The lesion involves the arm, back of the torso and leg. The patient reported no systemic symptoms. Present for about one day. The patient notes the lesion is flat. Female contributor, age 18–29. Symptoms reported: itching and bothersome appearance. Self-categorized by the patient as a rash. The photograph was taken at an angle — 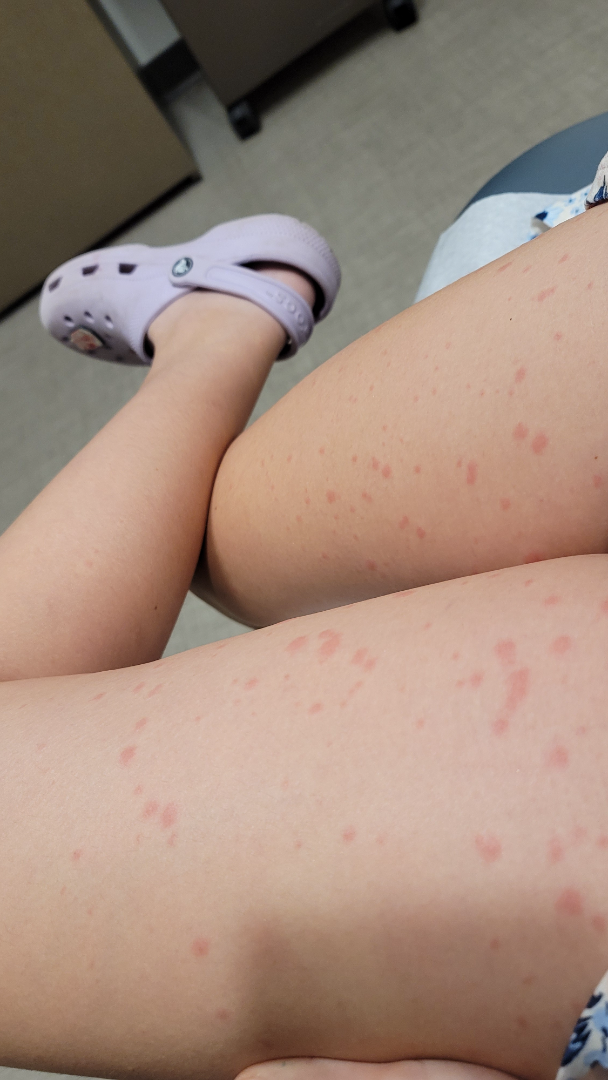dermatologist impression = Viral Exanthem and Drug Rash were each considered, in no particular order.